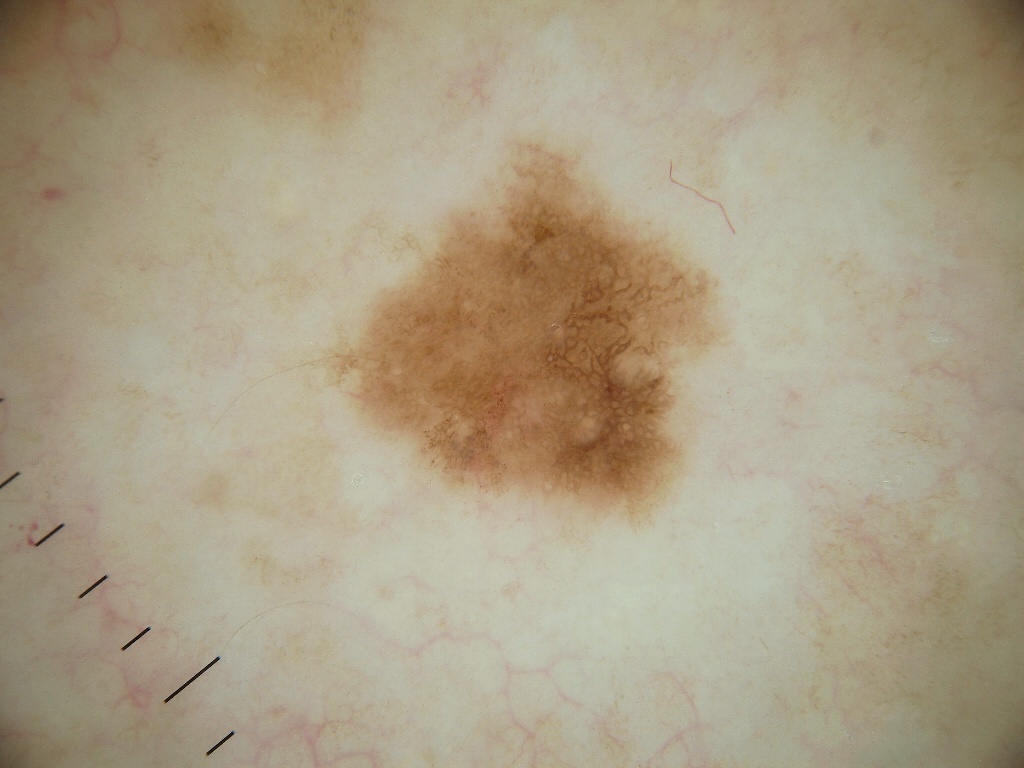| field | value |
|---|---|
| image type | dermatoscopic image of a skin lesion |
| subject | male, aged around 70 |
| dermoscopic findings | globules and pigment network; absent: negative network, milia-like cysts, and streaks |
| lesion location | x1=312, y1=135, x2=722, y2=520 |
| lesion size | moderate |
| assessment | a melanocytic nevus |